A dermoscopic close-up of a skin lesion.
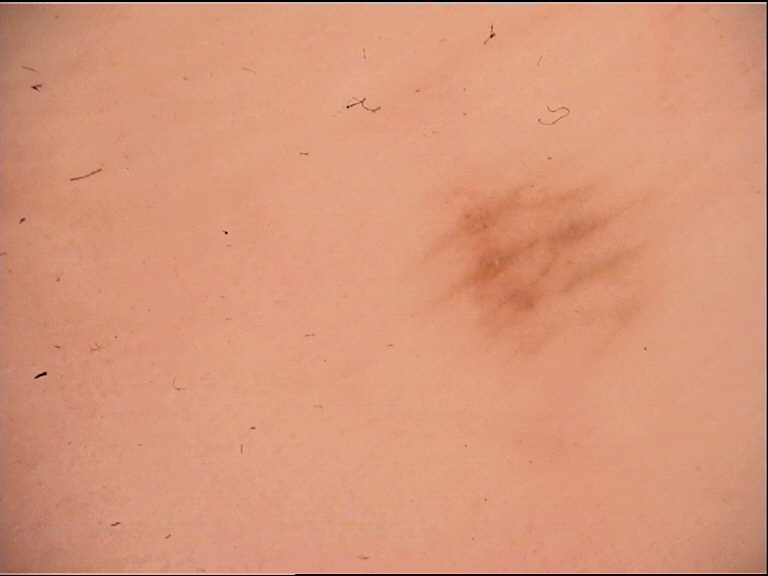Labeled as a banal lesion — an acral junctional nevus.